A dermoscopy image of a single skin lesion.
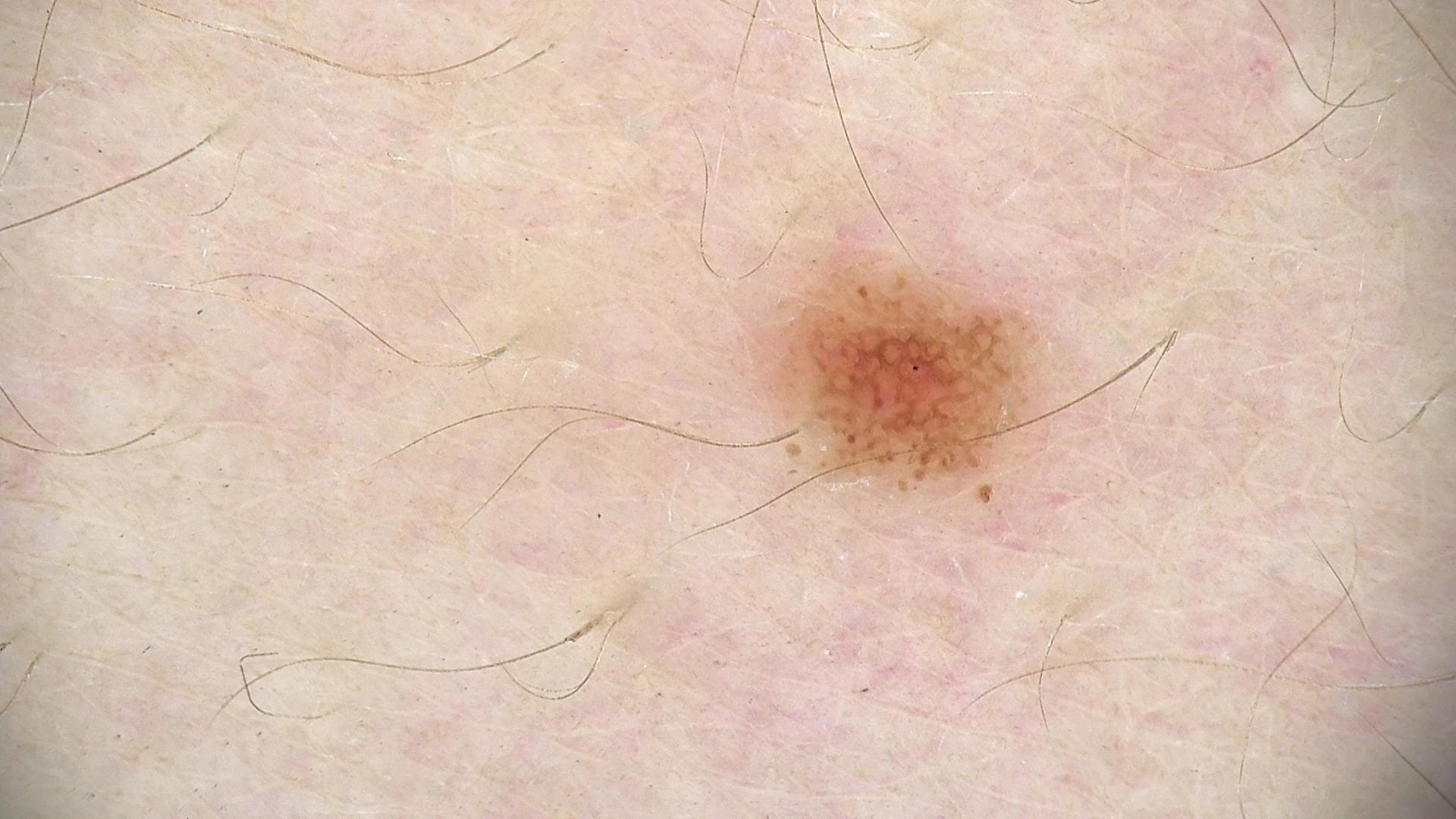Conclusion: The diagnostic label was a benign lesion — a dysplastic junctional nevus.